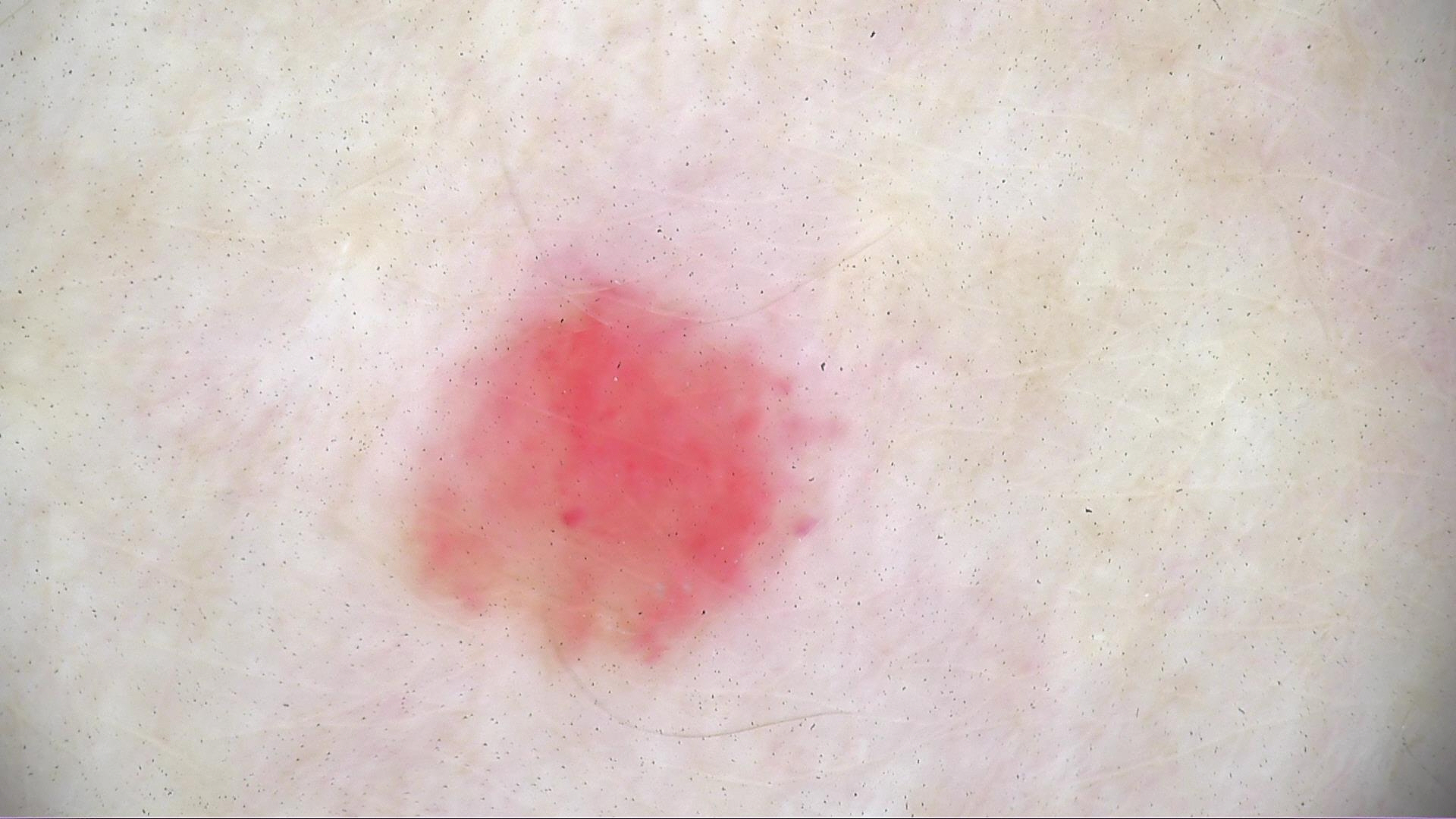diagnostic label: hemangioma (expert consensus).